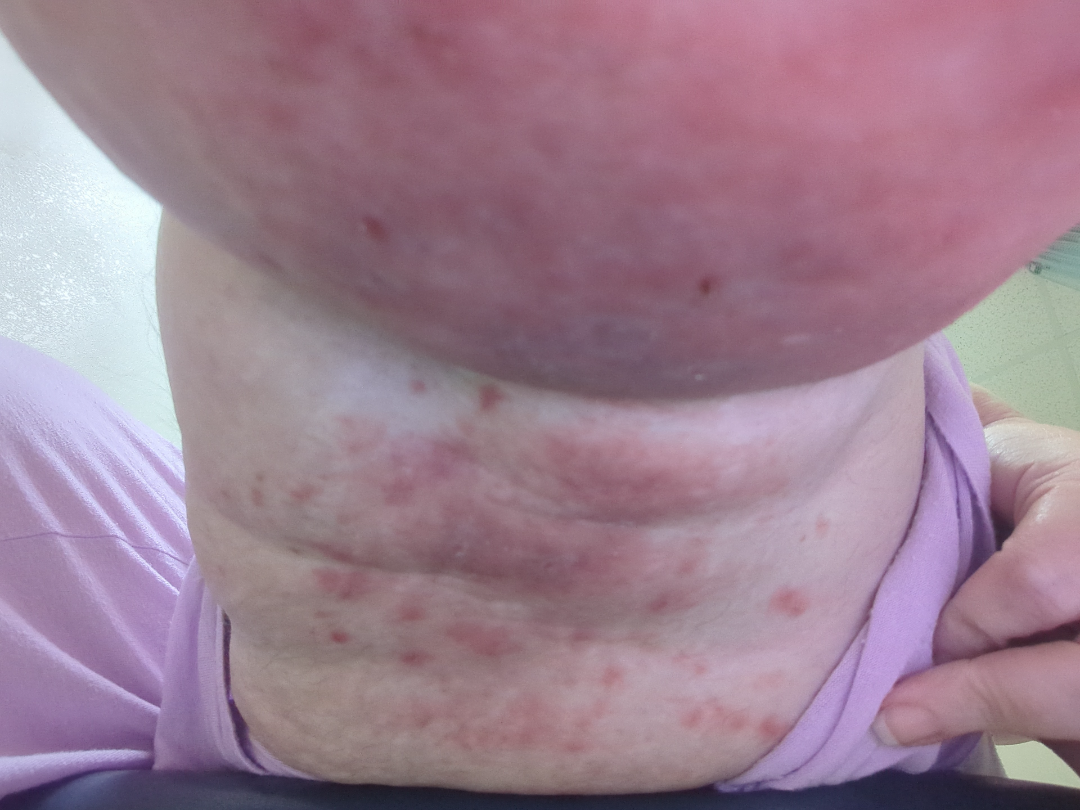Clinical context:
The affected area is the leg. The lesion is described as fluid-filled, rough or flaky and raised or bumpy. Present for one to four weeks. The contributor notes itching, enlargement and burning. Fitzpatrick skin type II. Female subject, age 40–49. The patient described the issue as a rash. A close-up photograph.
Assessment:
The leading consideration is Eczema; an alternative is Folliculitis; also on the differential is Hidradenitis; less likely is Irritant Contact Dermatitis.